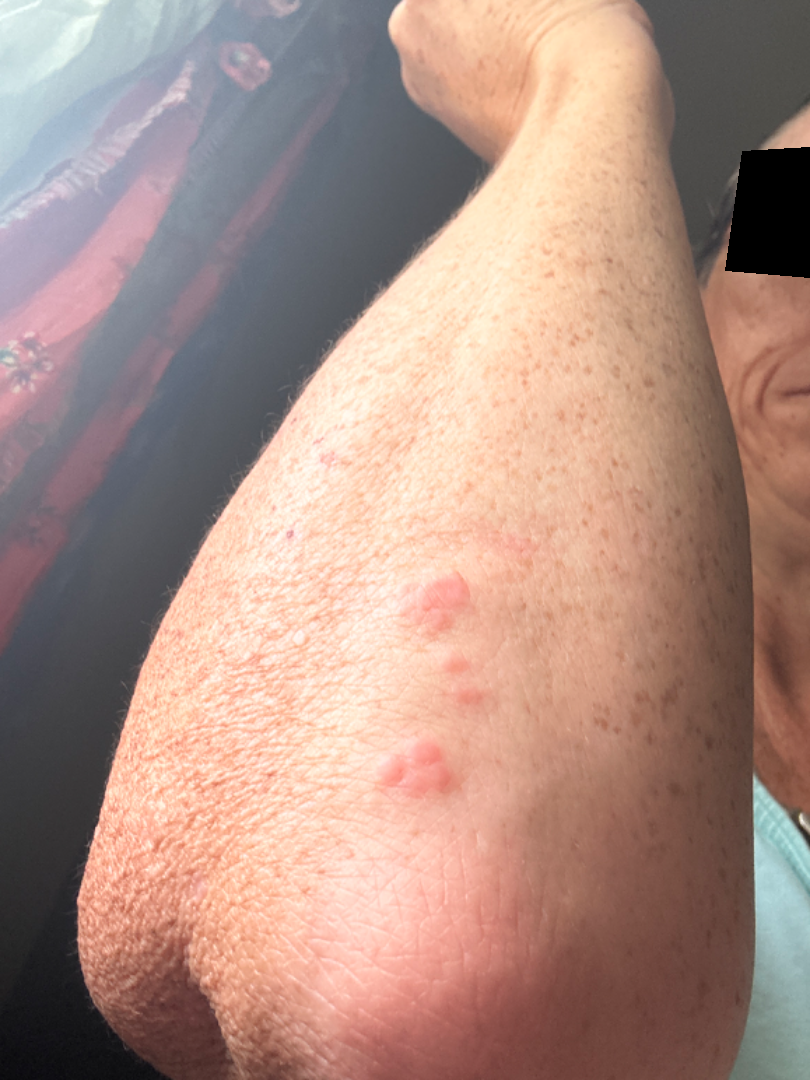{
  "duration": "more than one year",
  "body_site": "arm",
  "patient_category": "a rash",
  "systemic_symptoms": "none reported",
  "symptoms": [
    "bothersome appearance",
    "enlargement"
  ],
  "shot_type": "close-up",
  "differential": {
    "tied_lead": [
      "Granuloma annulare",
      "Insect Bite",
      "Allergic Contact Dermatitis"
    ]
  }
}